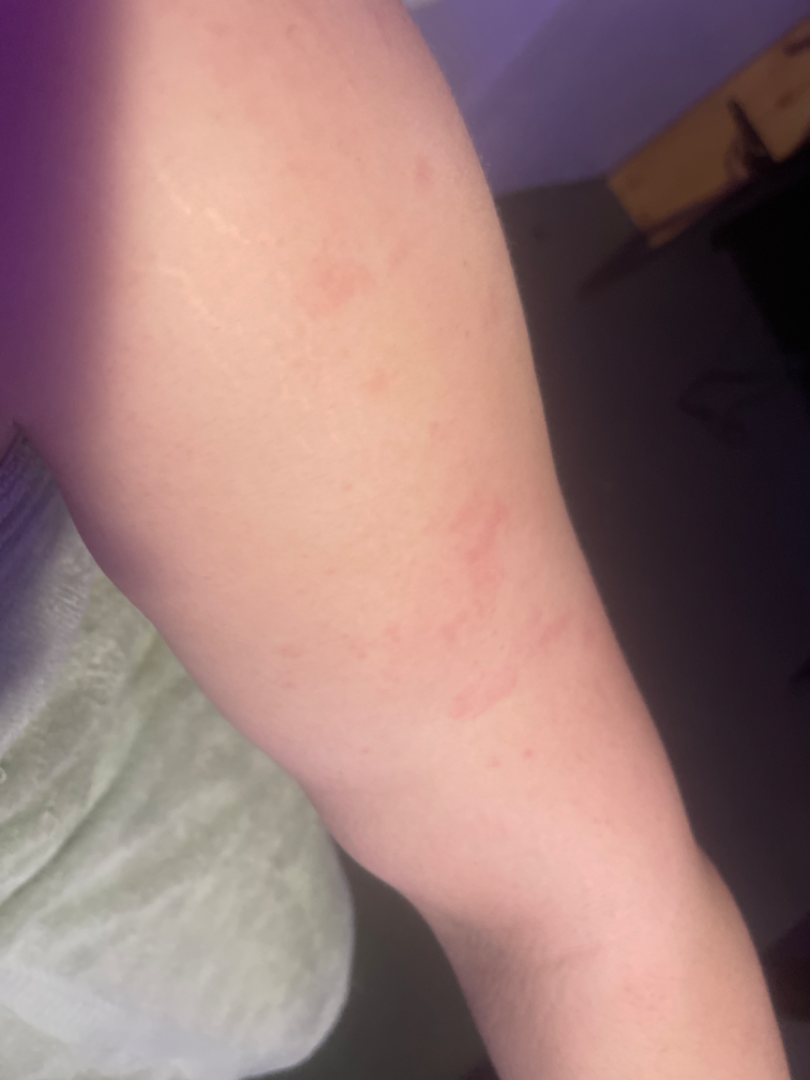Located on the front of the torso and arm. The photograph is a close-up of the affected area. Most likely Allergic Contact Dermatitis; an alternative is Urticaria.